The patient describes having few moles overall; acquired for a research image collection, with no referral diagnosis; the patient says their skin tans without first burning; a dermatoscopic image of a skin lesion — 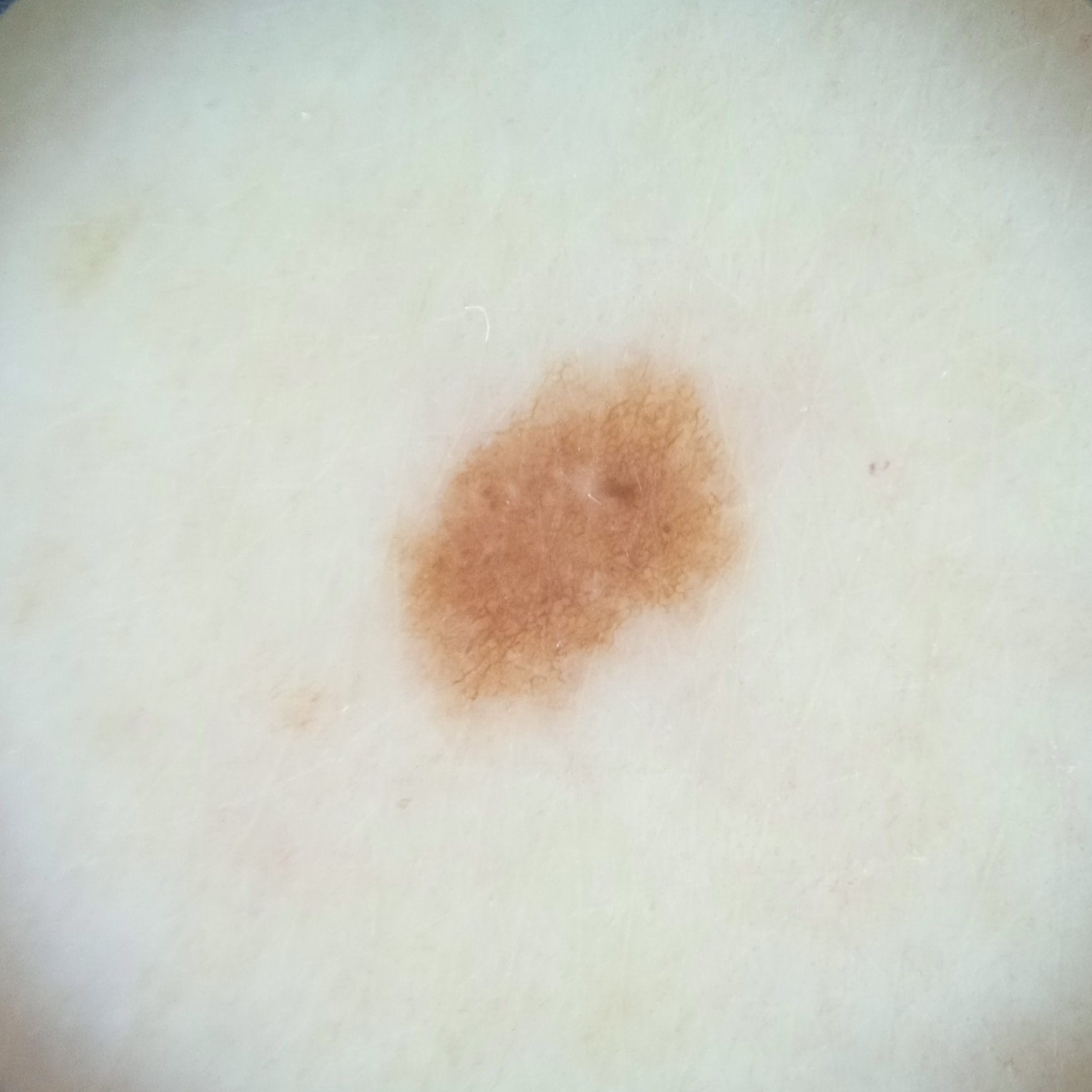<record>
<lesion_location>an arm</lesion_location>
<lesion_size>
<diameter_mm>4.9</diameter_mm>
</lesion_size>
<diagnosis>
<name>melanocytic nevus</name>
<malignancy>benign</malignancy>
</diagnosis>
</record>